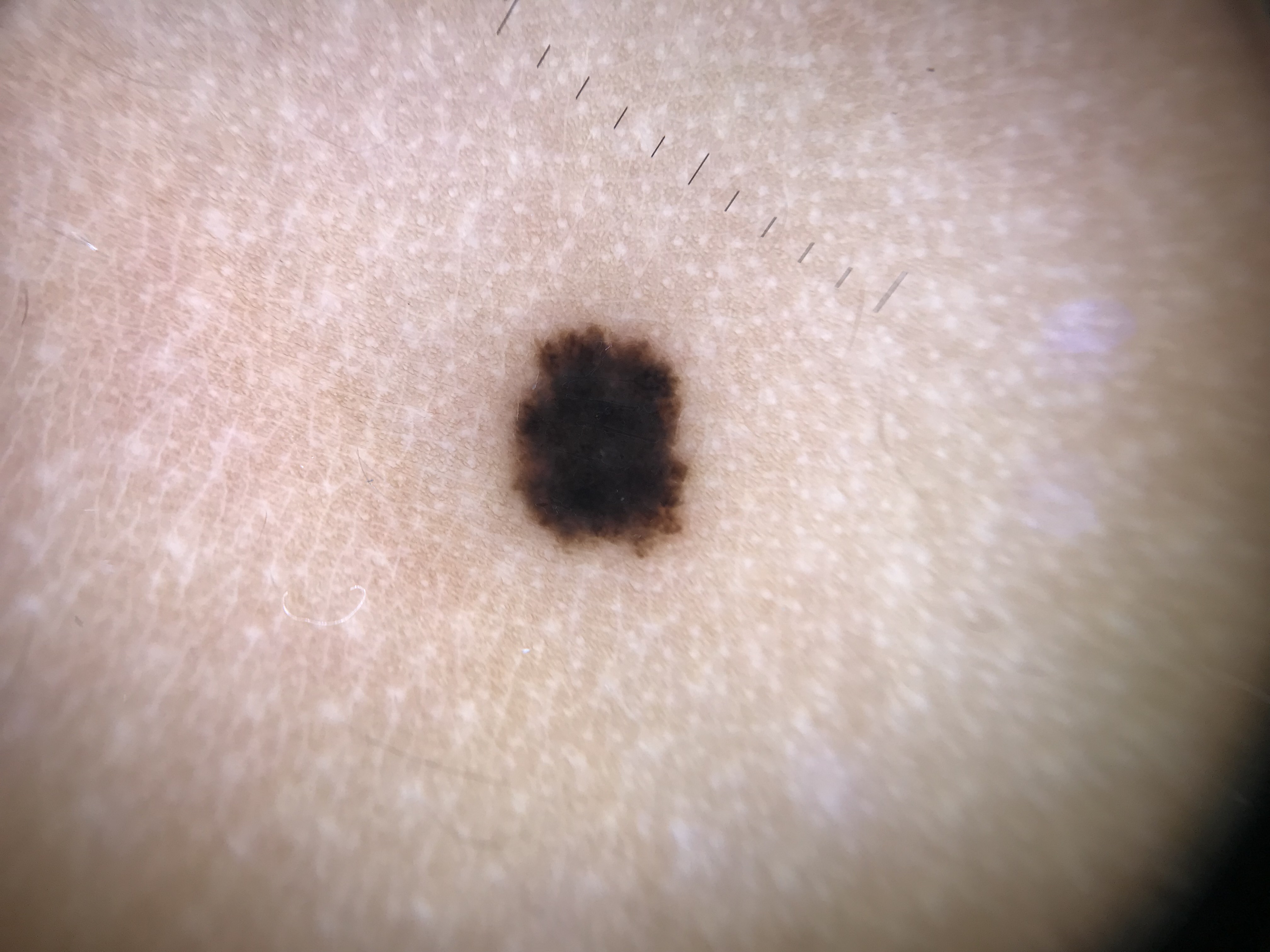A skin lesion imaged with a dermatoscope. The architecture is that of a dysplastic, junctional lesion. Labeled as a benign lesion — a Spitz/Reed nevus.